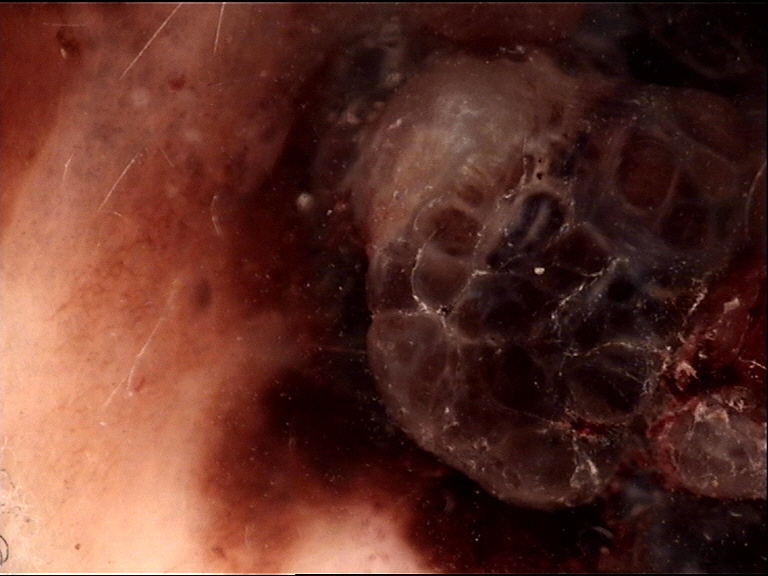A skin lesion imaged with a dermatoscope.
Confirmed on histopathology as a melanoma.